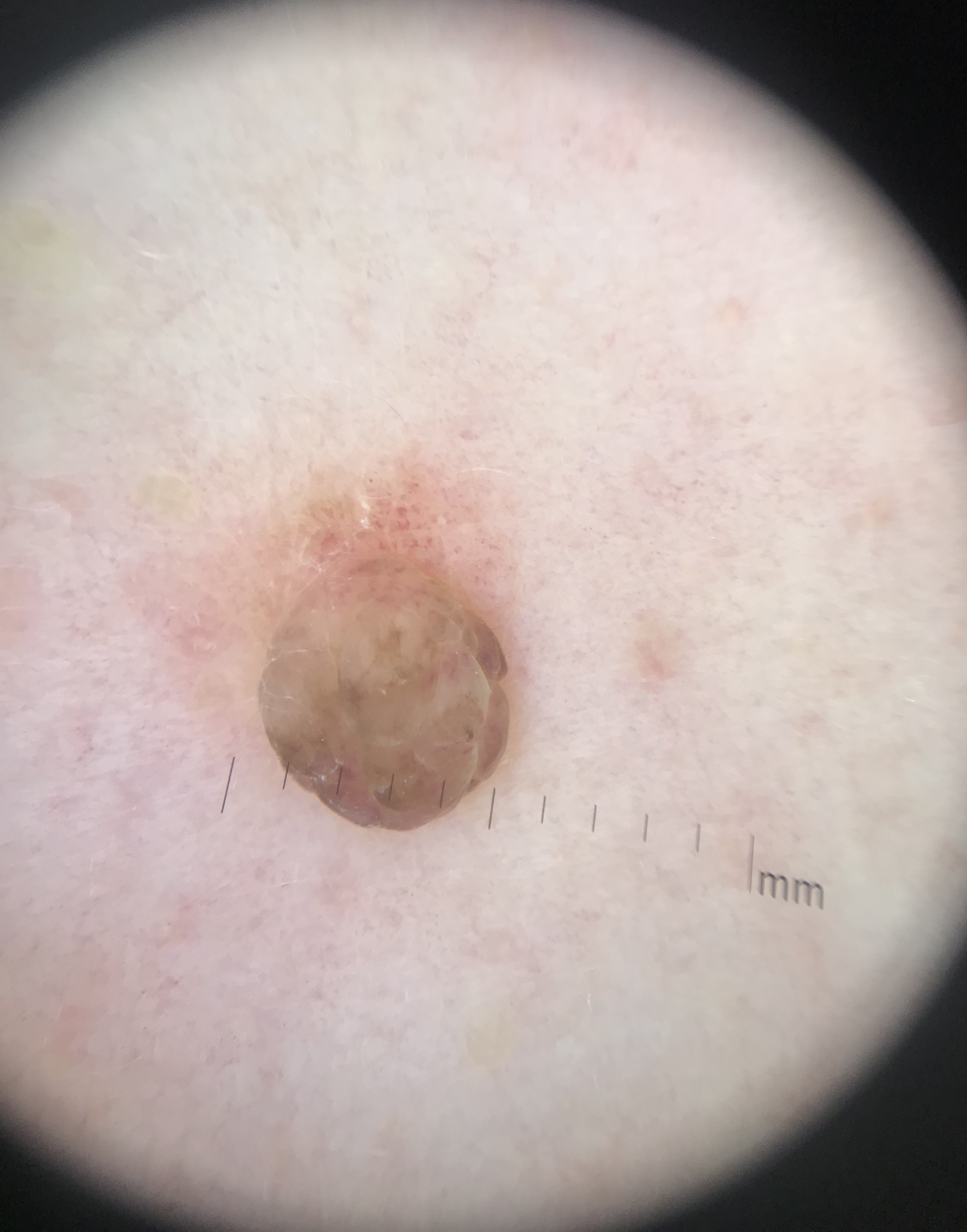label=dermal nevus (expert consensus).